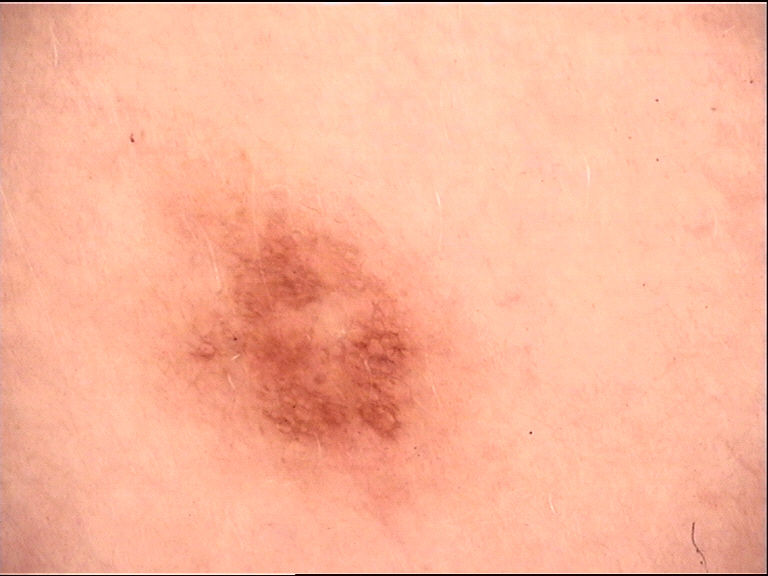diagnosis — dysplastic junctional nevus (expert consensus).